The affected area is the arm; the lesion is associated with itching; a close-up photograph; the patient reported no systemic symptoms; the contributor is male:
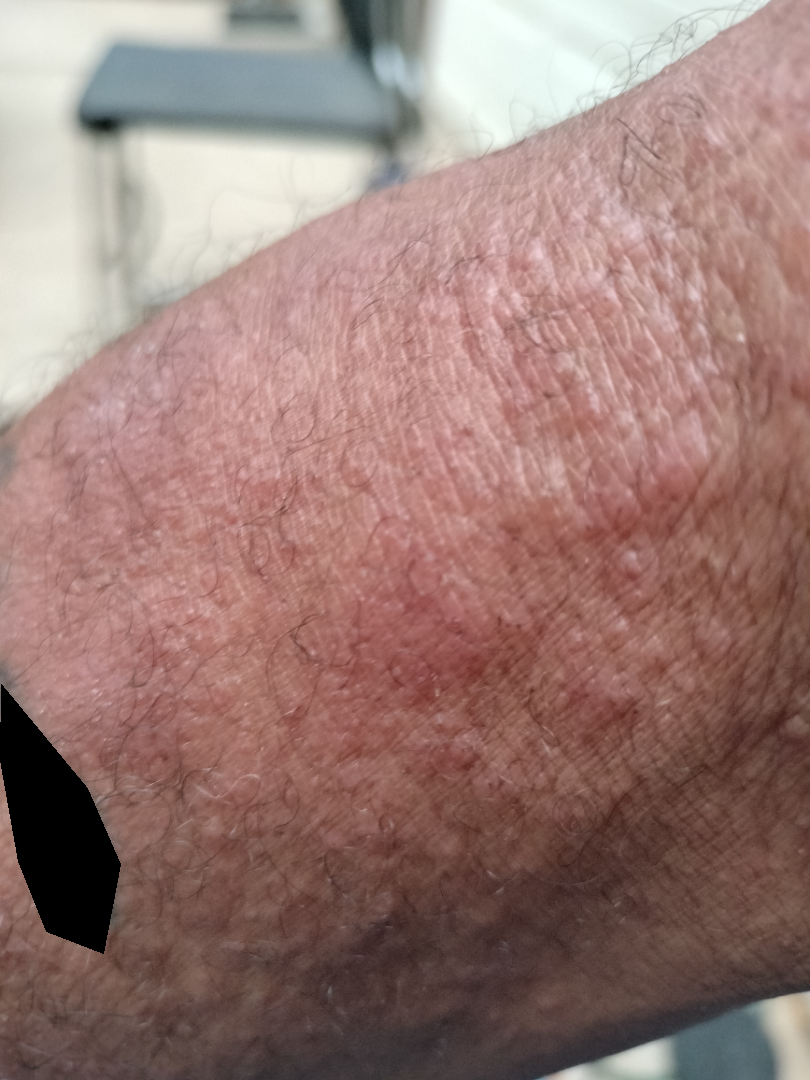| feature | finding |
|---|---|
| differential | the impression on review was Eczema |